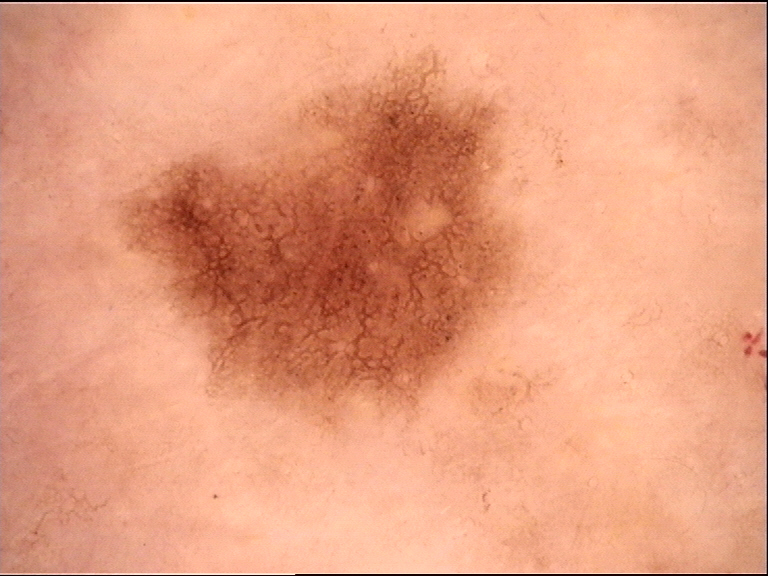image — dermoscopy
diagnostic label — dysplastic junctional nevus (expert consensus)